The lesion involves the arm; the contributor reports bothersome appearance; the photo was captured at a distance; the lesion is described as flat; skin tone: Fitzpatrick phototype III.
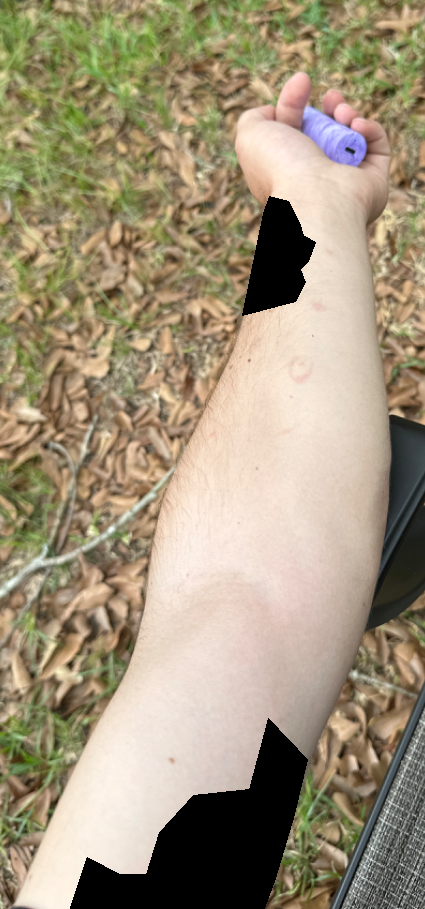Assessment: Diagnostic features were not clearly distinguishable in this photograph.